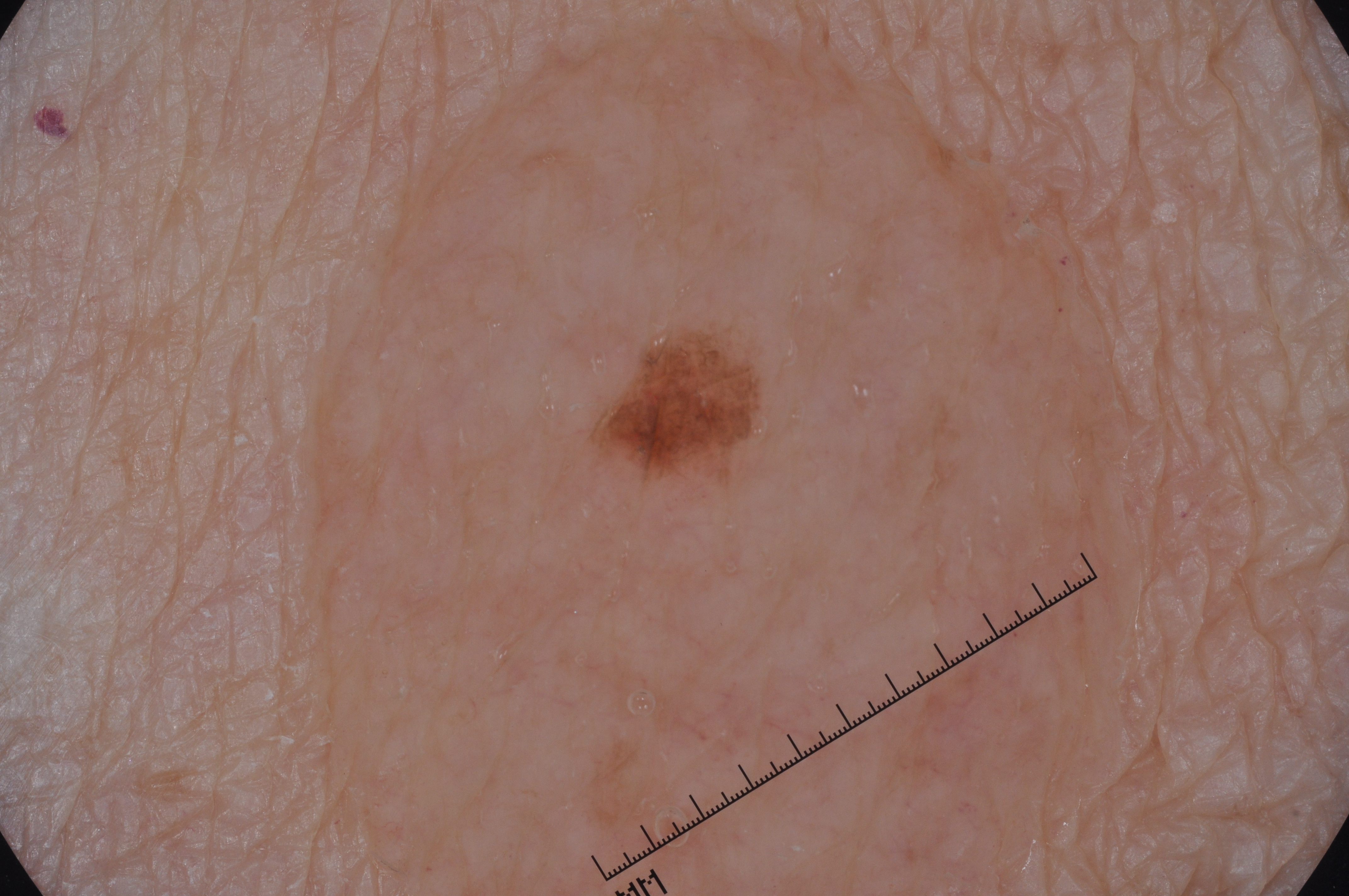Summary: A dermoscopic close-up of a skin lesion. A female subject aged 68-72. Dermoscopically, the lesion shows pigment network. The lesion is located at left=575, top=320, right=769, bottom=494. Impression: Consistent with a melanocytic nevus.